A patient in their 70s:
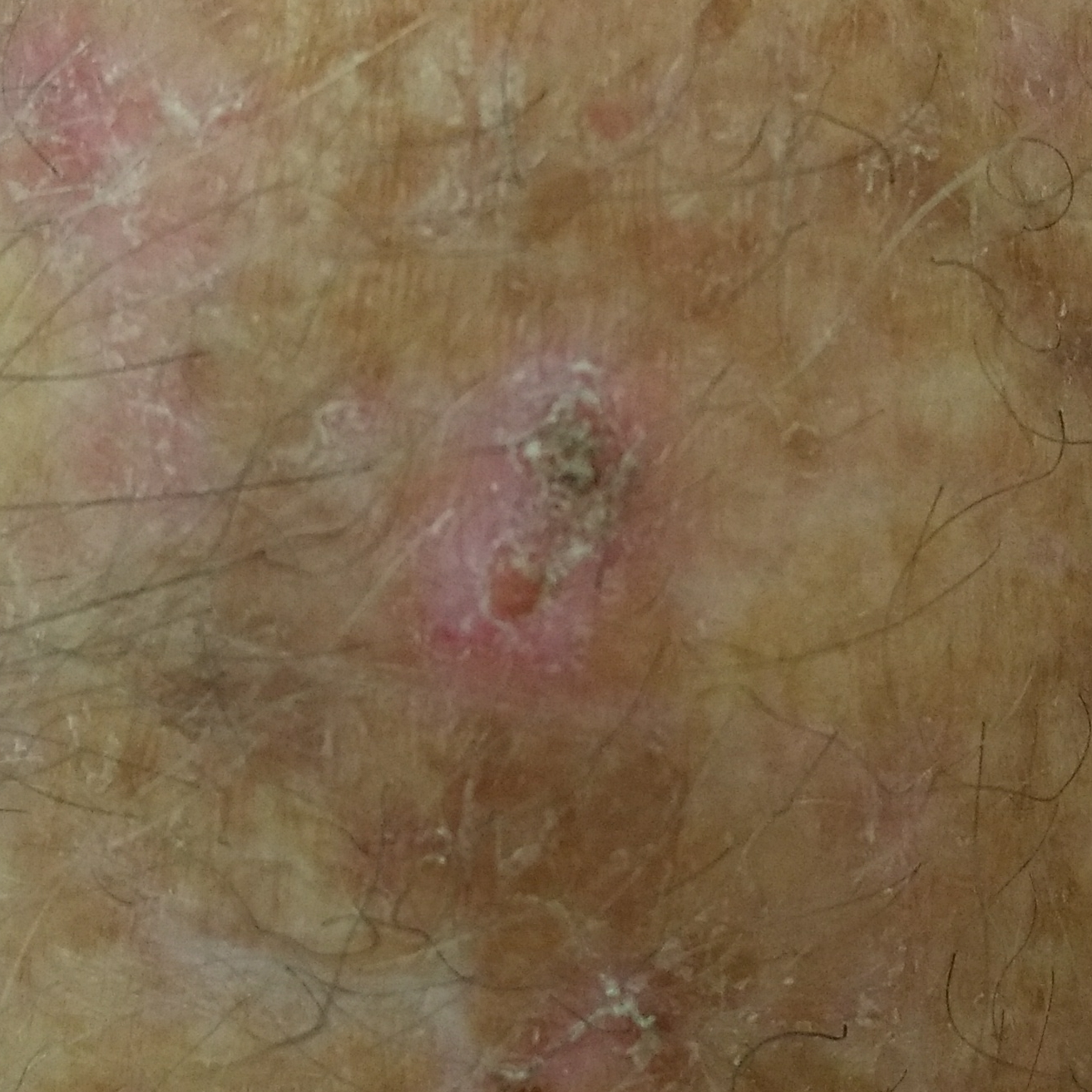<record>
<lesion_location>a forearm</lesion_location>
<symptoms>
<present>elevation, growth</present>
<absent>change in appearance</absent>
</symptoms>
<diagnosis>
<name>actinic keratosis</name>
<code>ACK</code>
<malignancy>indeterminate</malignancy>
<confirmation>clinical consensus</confirmation>
</diagnosis>
</record>